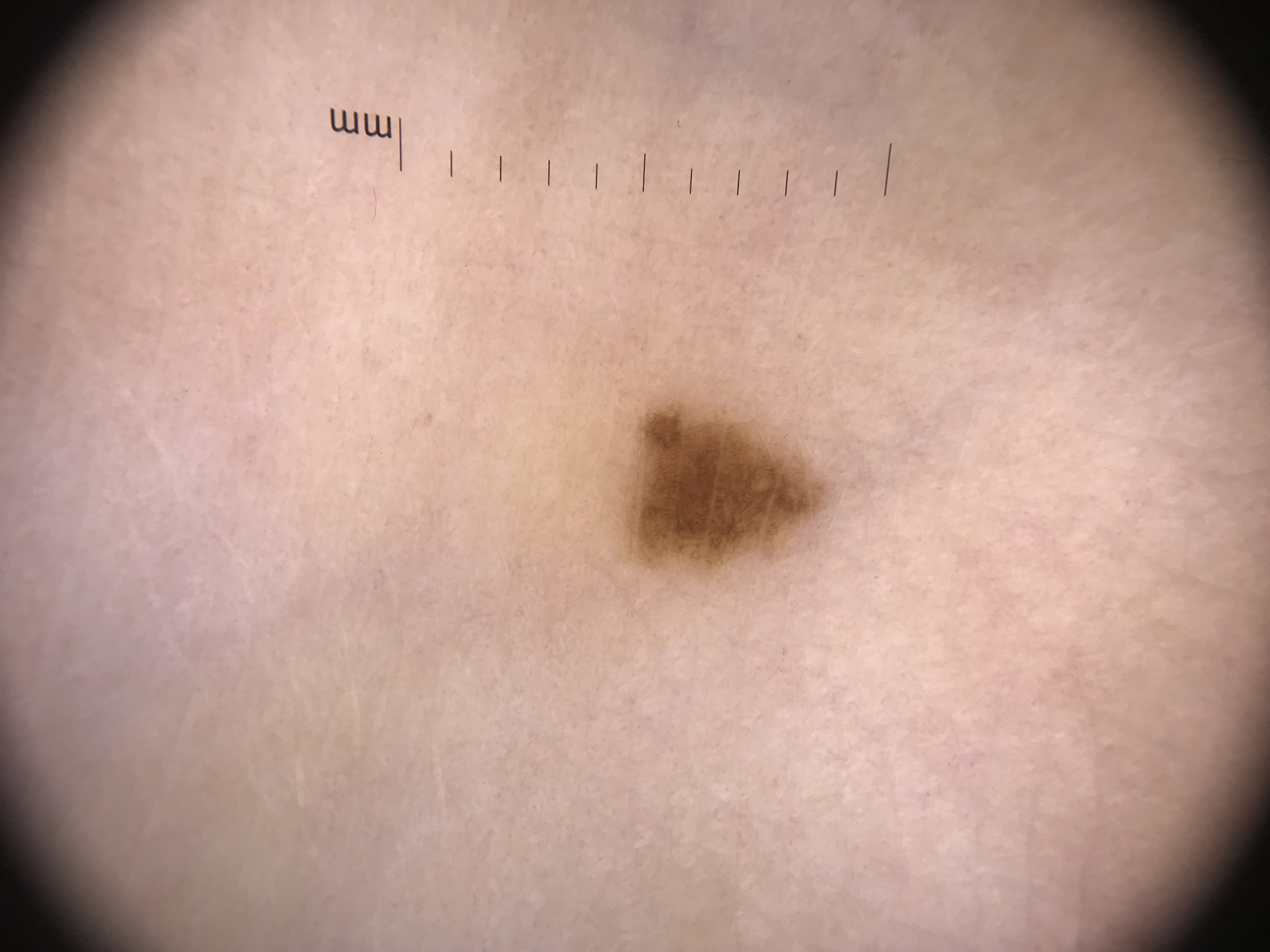Consistent with a dysplastic junctional nevus.